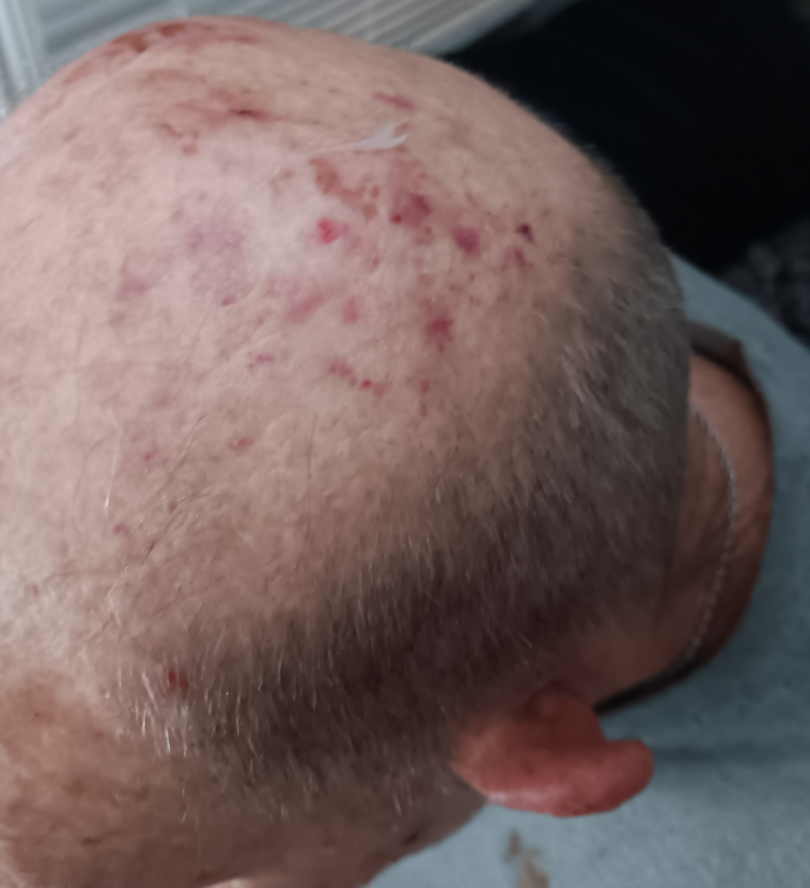Case summary:
* assessment: could not be assessed
* framing: at an angle